Texture is reported as flat · reported duration is about one day · located on the leg · the patient reported no systemic symptoms · an image taken at an angle · the patient considered this a rash: 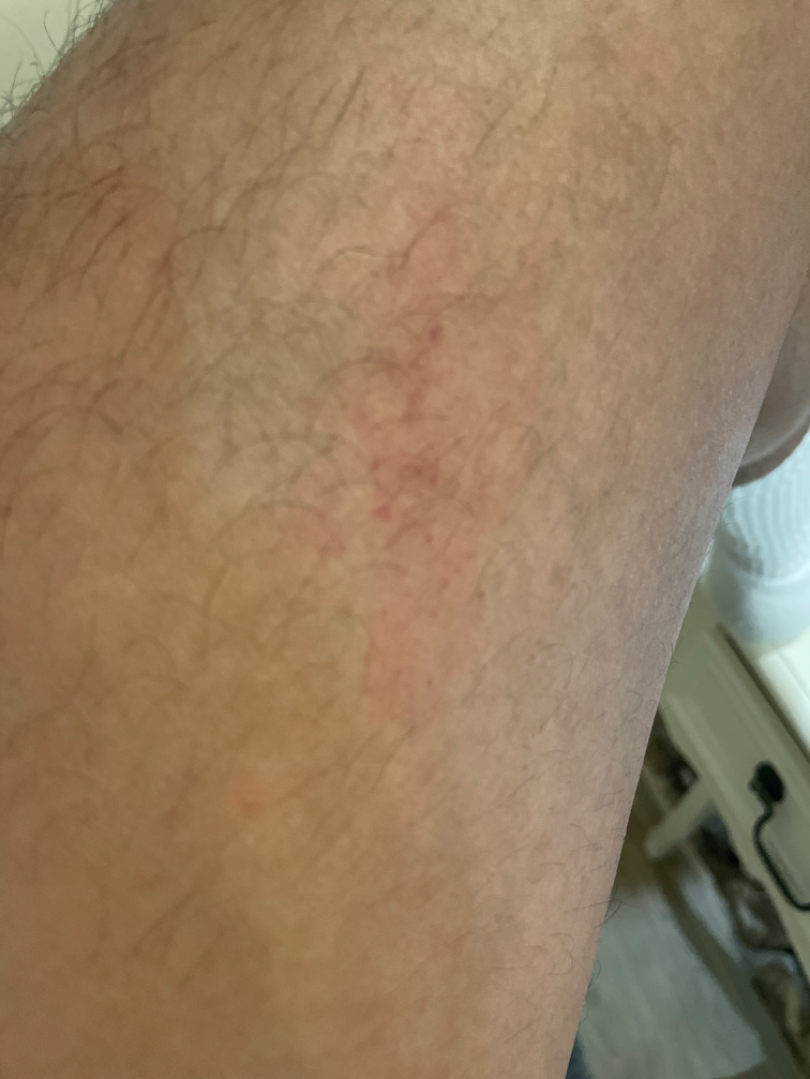Review: No differential diagnosis could be assigned on photographic review.